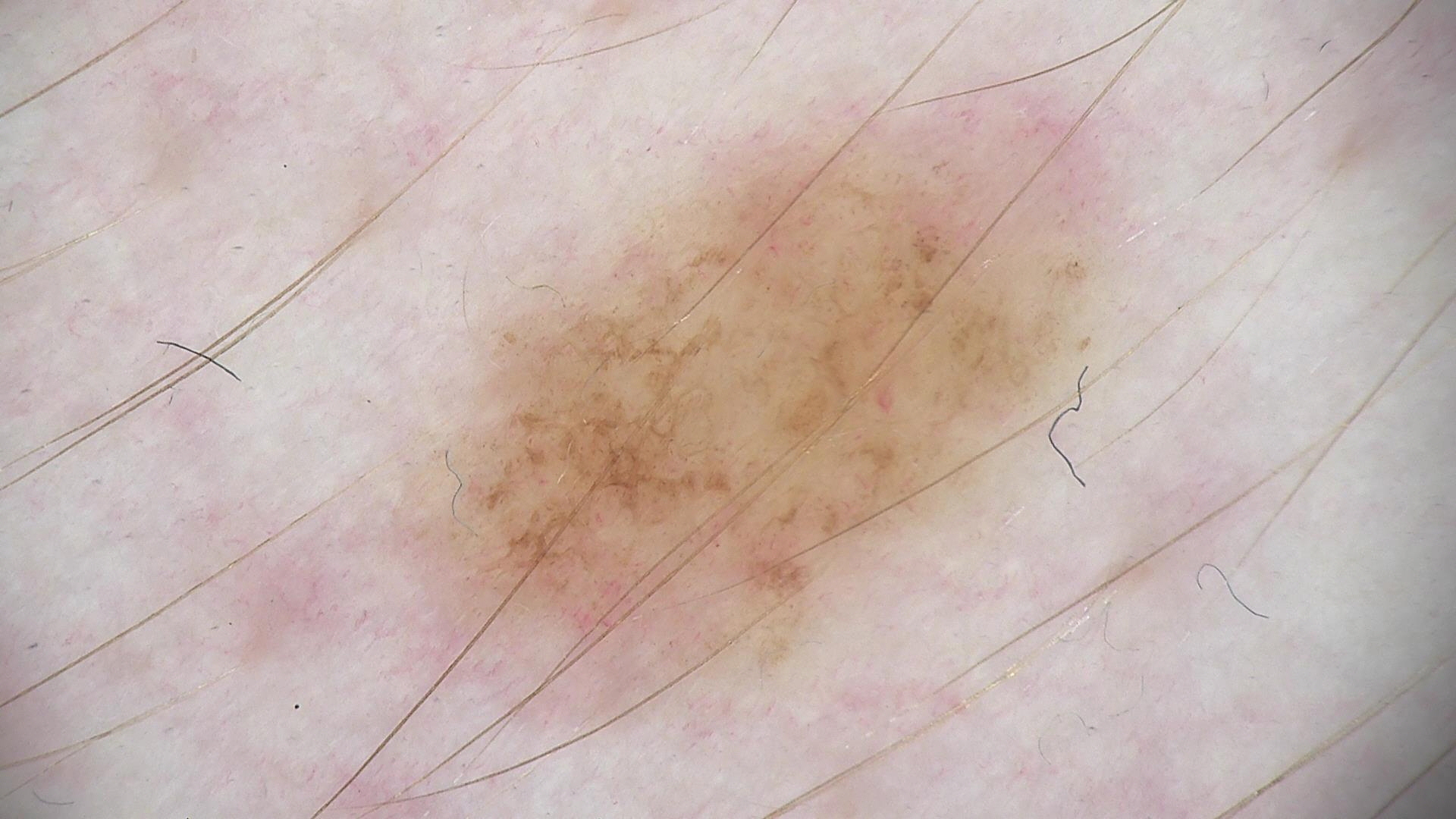A dermoscopy image of a single skin lesion.
Consistent with a benign lesion — a dysplastic junctional nevus.